This is a close-up image, the lesion involves the front of the torso and back of the torso, skin tone: Fitzpatrick skin type I; lay graders estimated Monk skin tone scale 4 (US pool) or 2 (India pool):
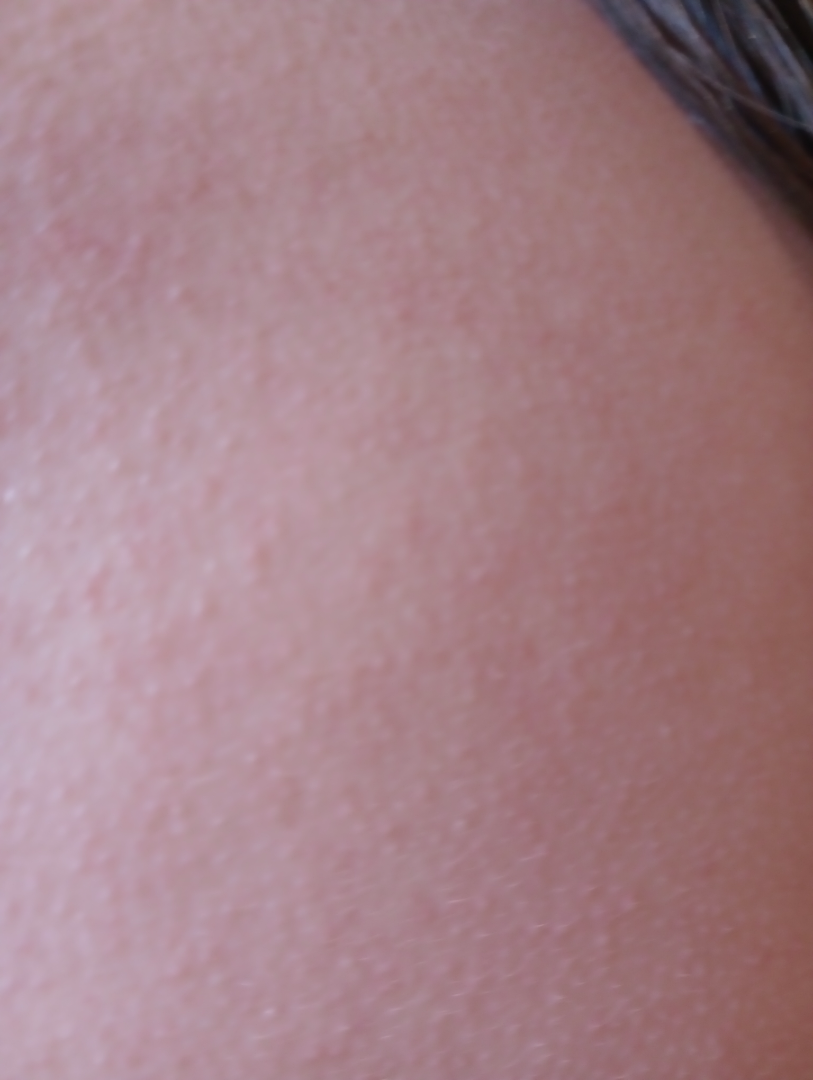Impression: The reviewing clinician's impression was: Keratosis pilaris (54%); Lichen spinulosus (23%); Eczema (23%).